Male contributor, age 18–29 · the lesion involves the leg · symptoms reported: enlargement and itching · the photograph is a close-up of the affected area — 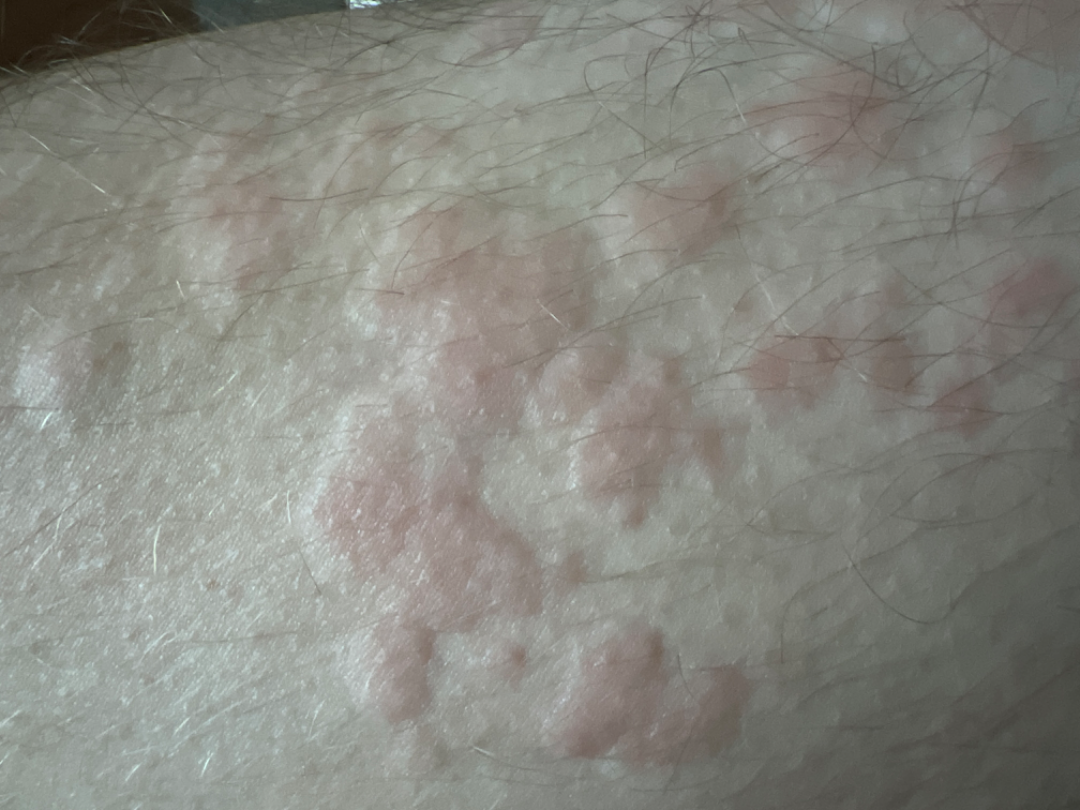Reviewed remotely by one dermatologist: most consistent with Urticaria.